The lesion is described as flat. The patient reports associated fatigue. Self-categorized by the patient as a rash. No associated lesion symptoms were reported. The photo was captured at a distance. Located on the back of the torso and front of the torso. The subject is 18–29, male:
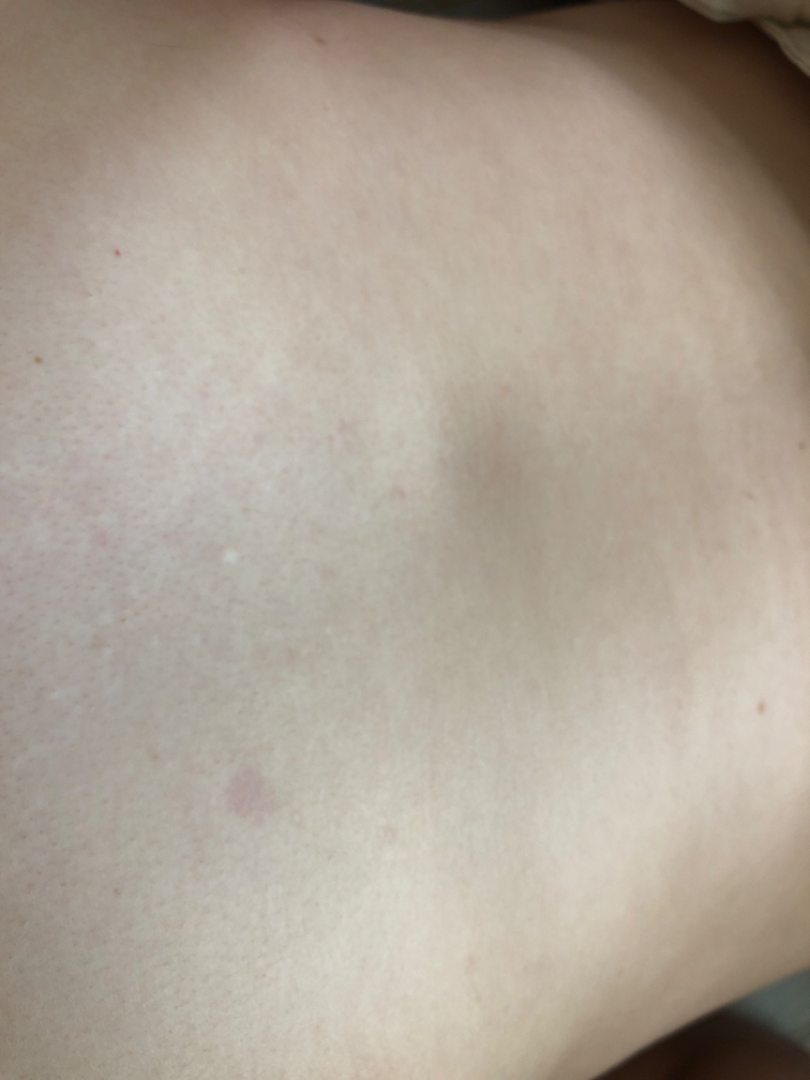assessment=could not be assessed